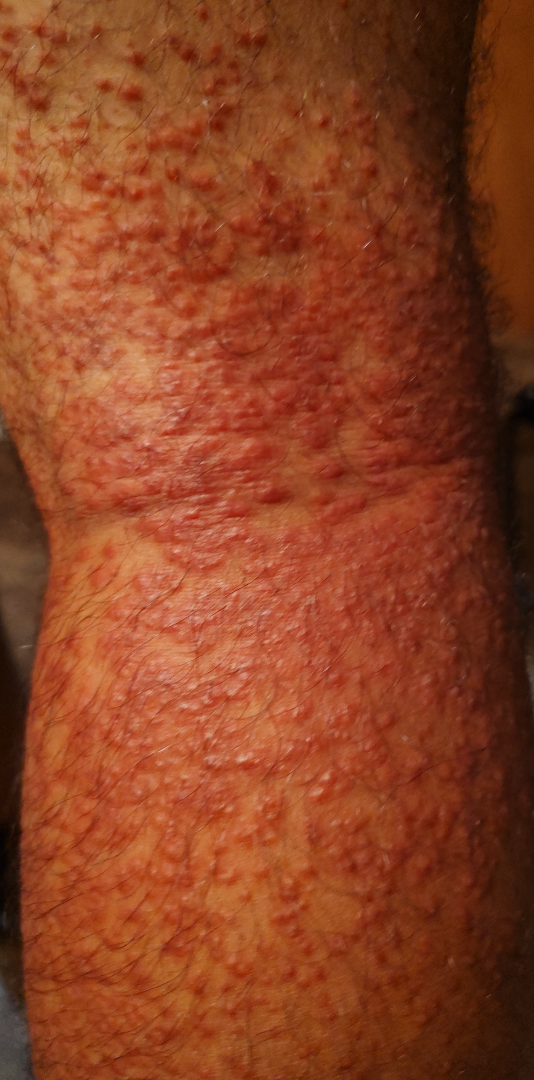A close-up photograph. Texture is reported as rough or flaky and raised or bumpy. Most consistent with Lichen planus/lichenoid eruption; also consider Hypersensitivity; less probable is Eczema.